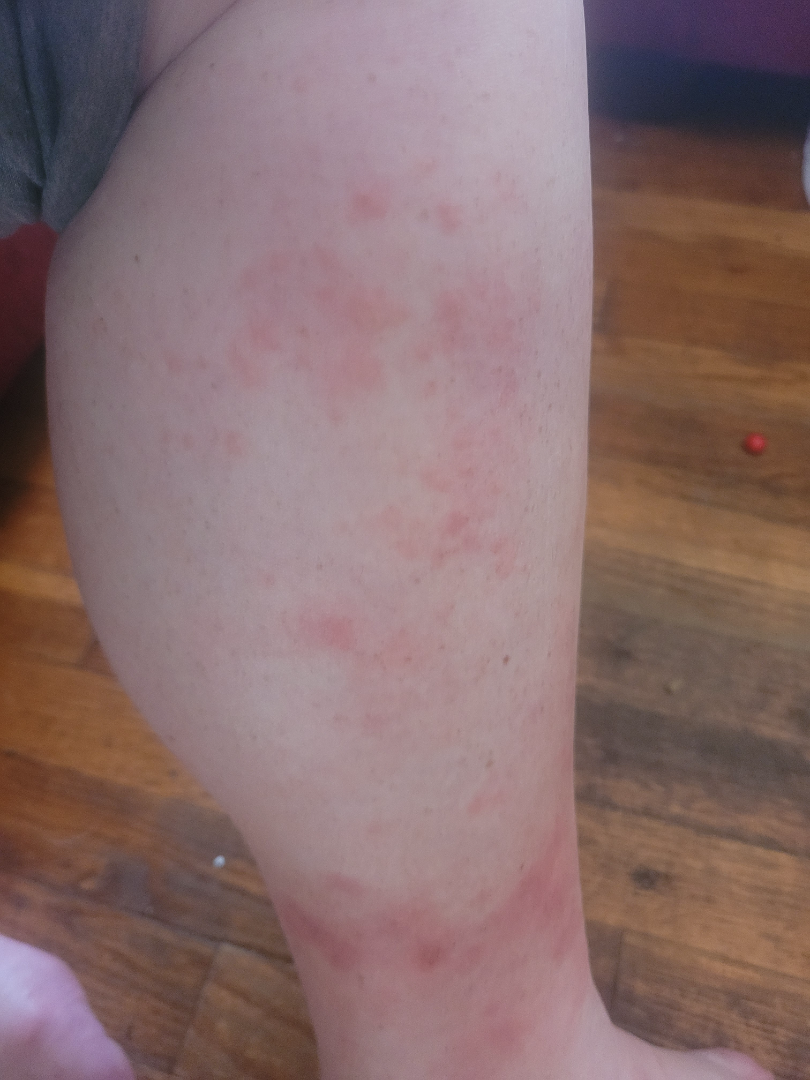Clinical context:
The affected area is the leg. The contributor is 40–49, female. The patient considered this a rash. This image was taken at an angle. The condition has been present for less than one week. The contributor reports the lesion is raised or bumpy. Symptoms reported: darkening, itching, enlargement and bothersome appearance. The patient reported no systemic symptoms.
Assessment:
The differential includes Stasis Dermatitis, Eczema and Allergic Contact Dermatitis, with no clear leading consideration.